This image was taken at an angle; the patient is a male aged 30–39; the affected area is the leg — 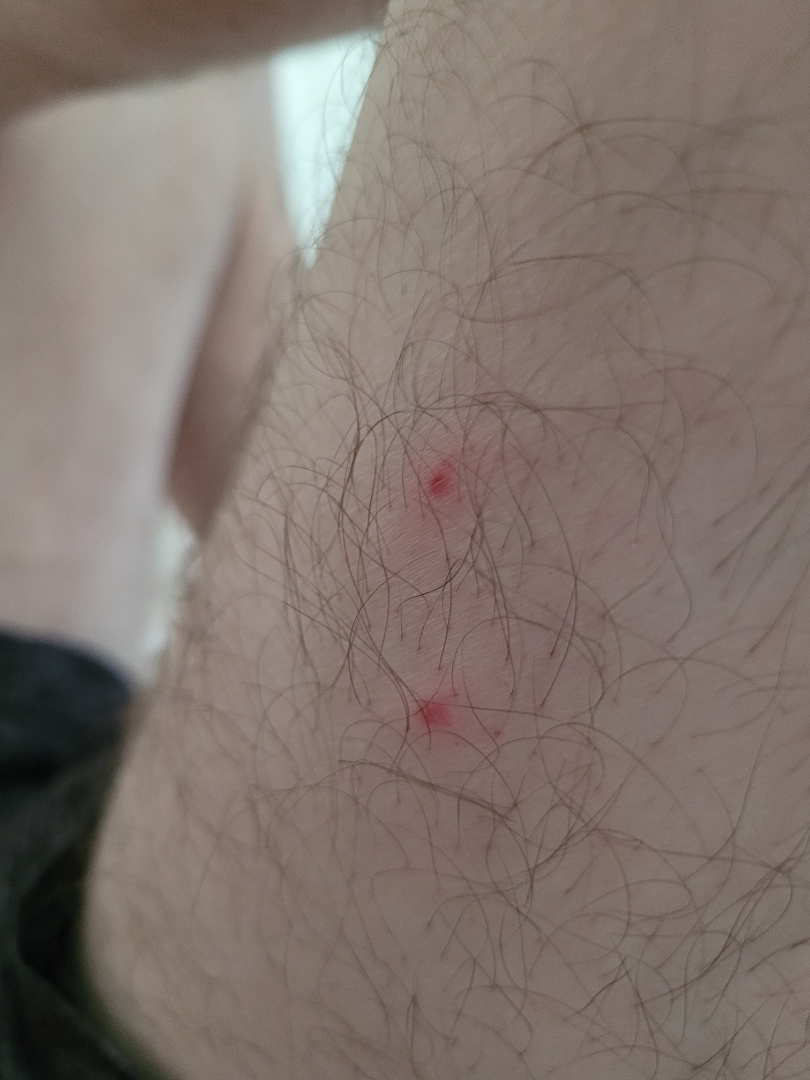| field | value |
|---|---|
| assessment | could not be assessed |
| symptoms | itching |
| onset | less than one week |
| skin tone | FST III; non-clinician graders estimated a MST of 2 |
| patient's own categorization | a rash |
| texture | raised or bumpy |